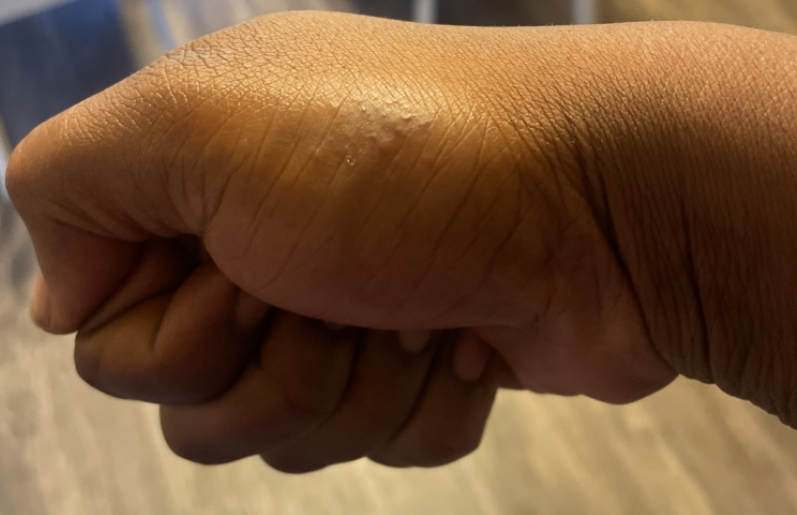assessment: could not be assessed
duration: less than one week
body_site: back of the hand
systemic_symptoms: none reported
symptoms: itching
shot_type: at an angle
patient_category: a rash
texture: raised or bumpy
patient: male, age 18–29